A skin lesion imaged with a dermatoscope.
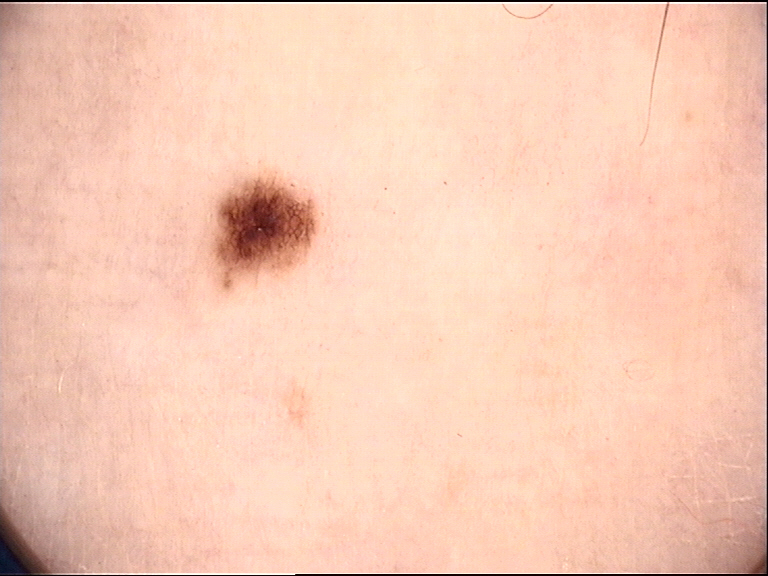Conclusion:
Labeled as a dysplastic junctional nevus.